The contributor is 18–29, male · the arm is involved · the photo was captured at a distance: 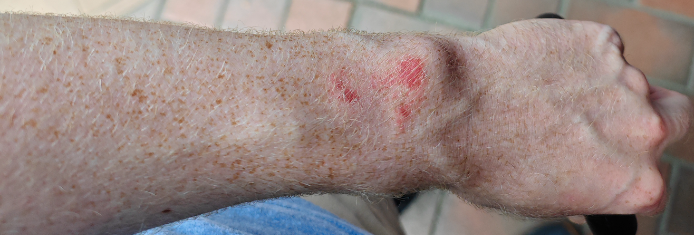Clinical context:
The condition has been present for one to four weeks. The patient notes the lesion is rough or flaky. The patient notes bothersome appearance and itching. Fitzpatrick skin type I. The patient described the issue as a rash.
Assessment:
On remote dermatologist review: the leading impression is Superficial wound of body region; the differential also includes SCC/SCCIS.